The contributor reports the condition has been present for one to four weeks · self-categorized by the patient as a rash · the lesion involves the palm, back of the hand and arm · texture is reported as rough or flaky, raised or bumpy and fluid-filled · close-up view:
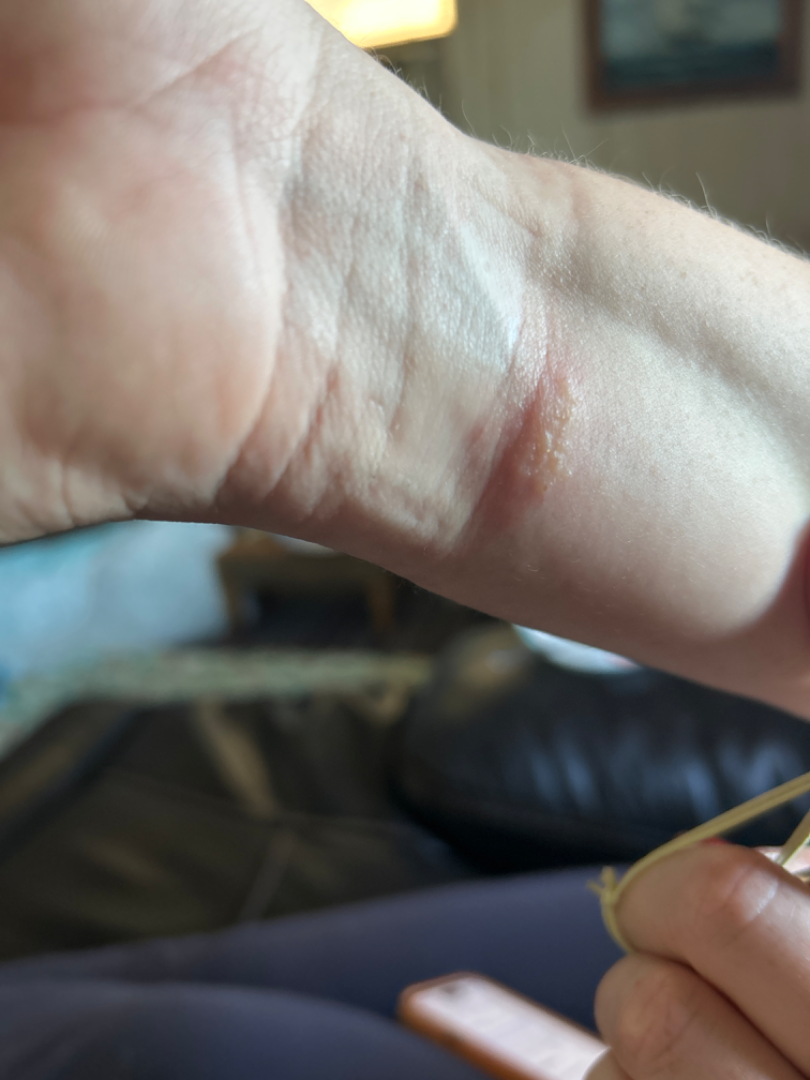{"differential": {"leading": ["Allergic Contact Dermatitis"], "considered": ["Impetigo", "Eczema"]}}